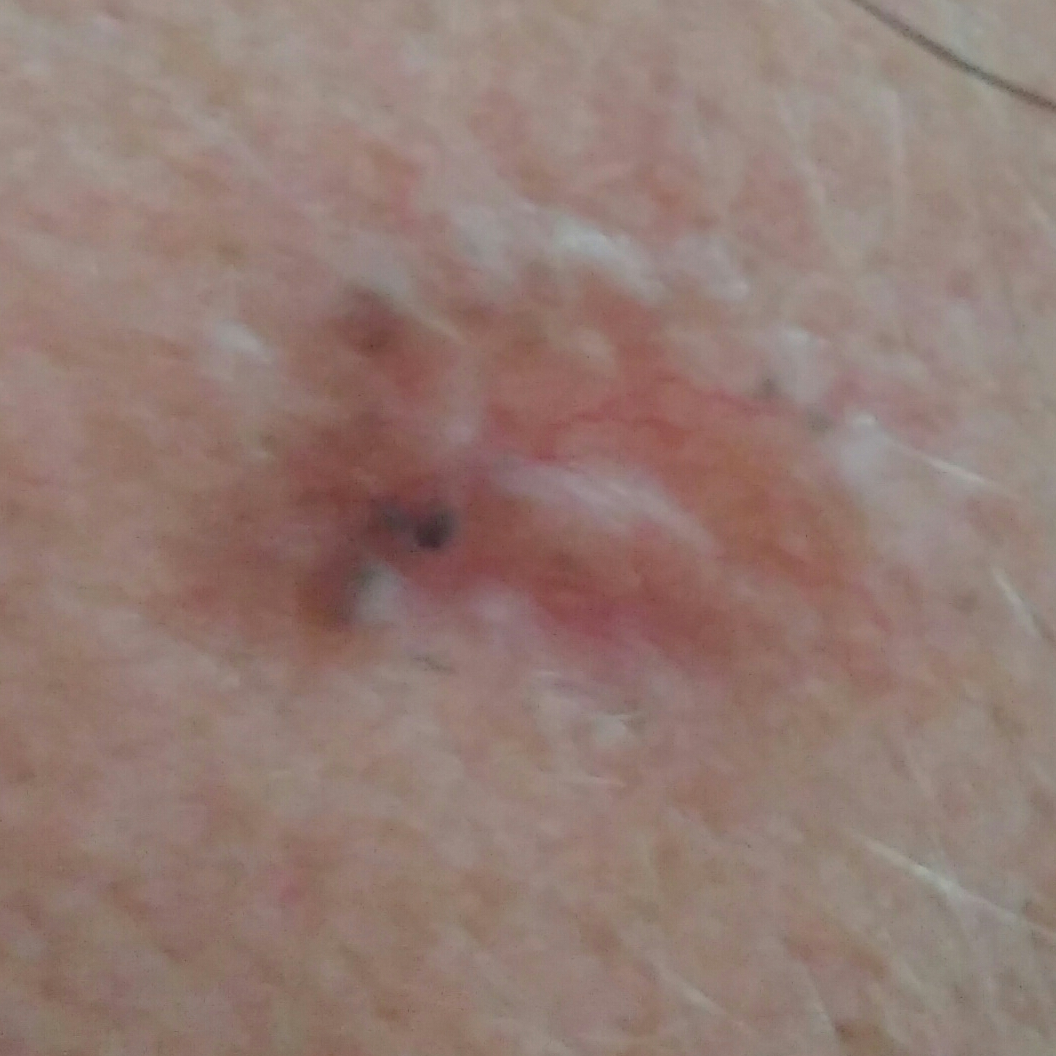diagnostic label: basal cell carcinoma (biopsy-proven)